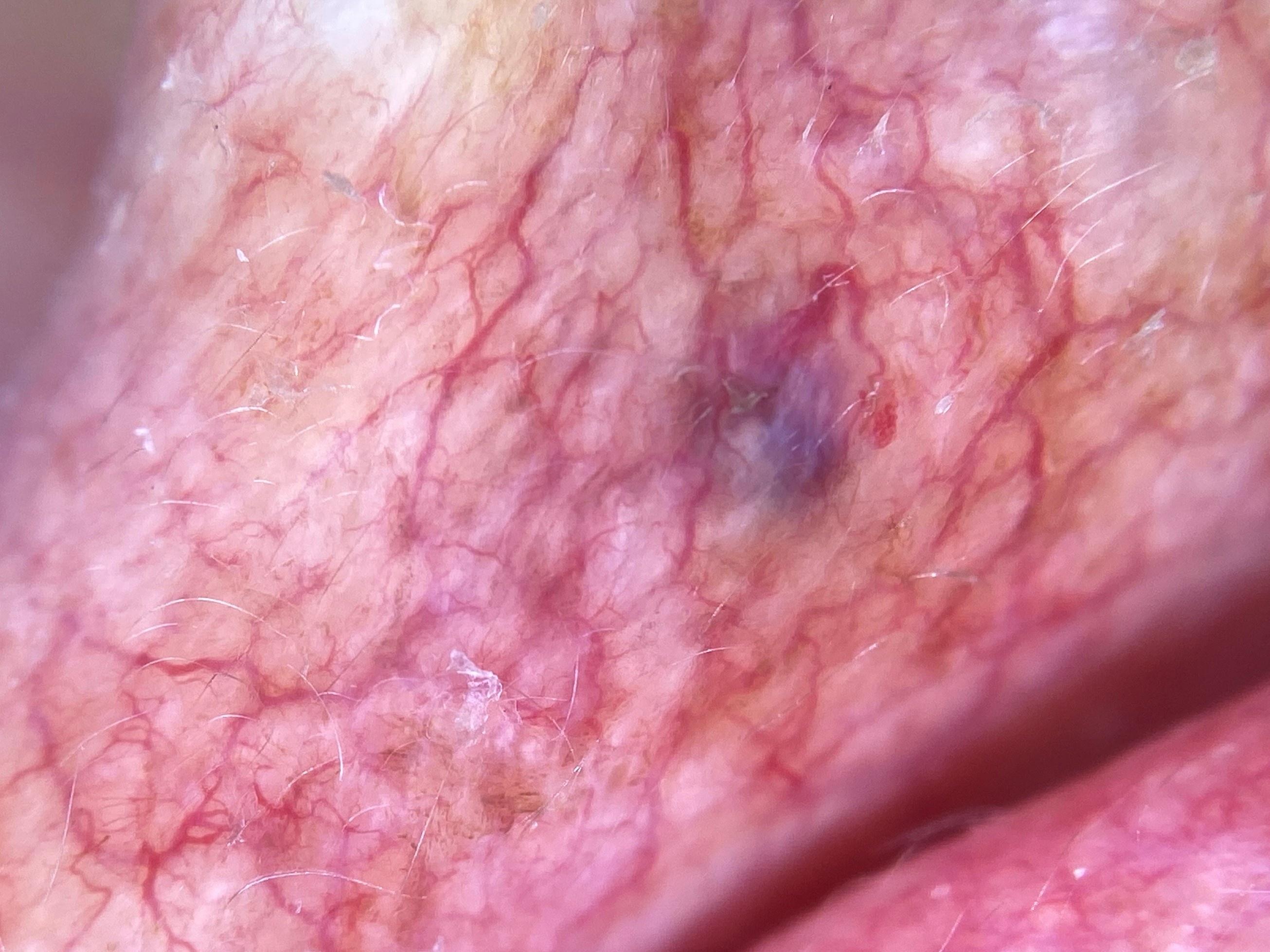A male patient aged approximately 75.
A skin lesion imaged with contact-polarized dermoscopy.
The lesion was found on the head or neck.
The clinical impression was a vascular lesion.